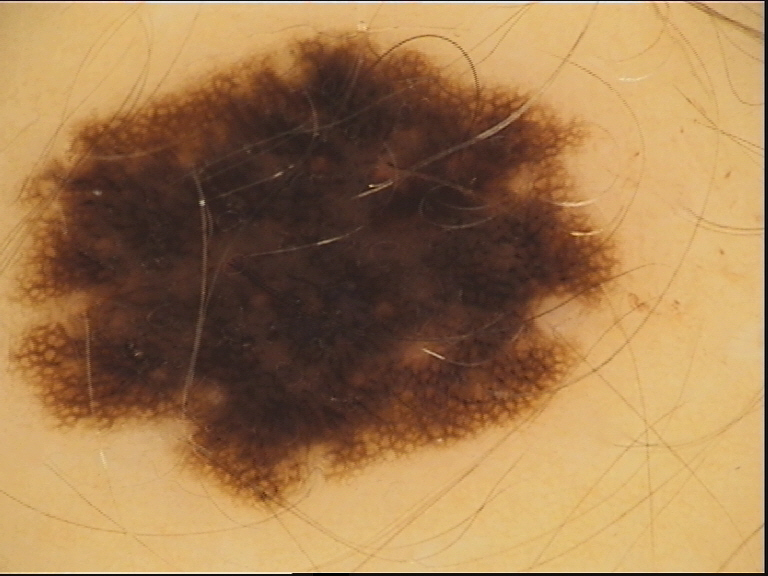A dermoscopy image of a single skin lesion. Labeled as a dysplastic compound nevus.